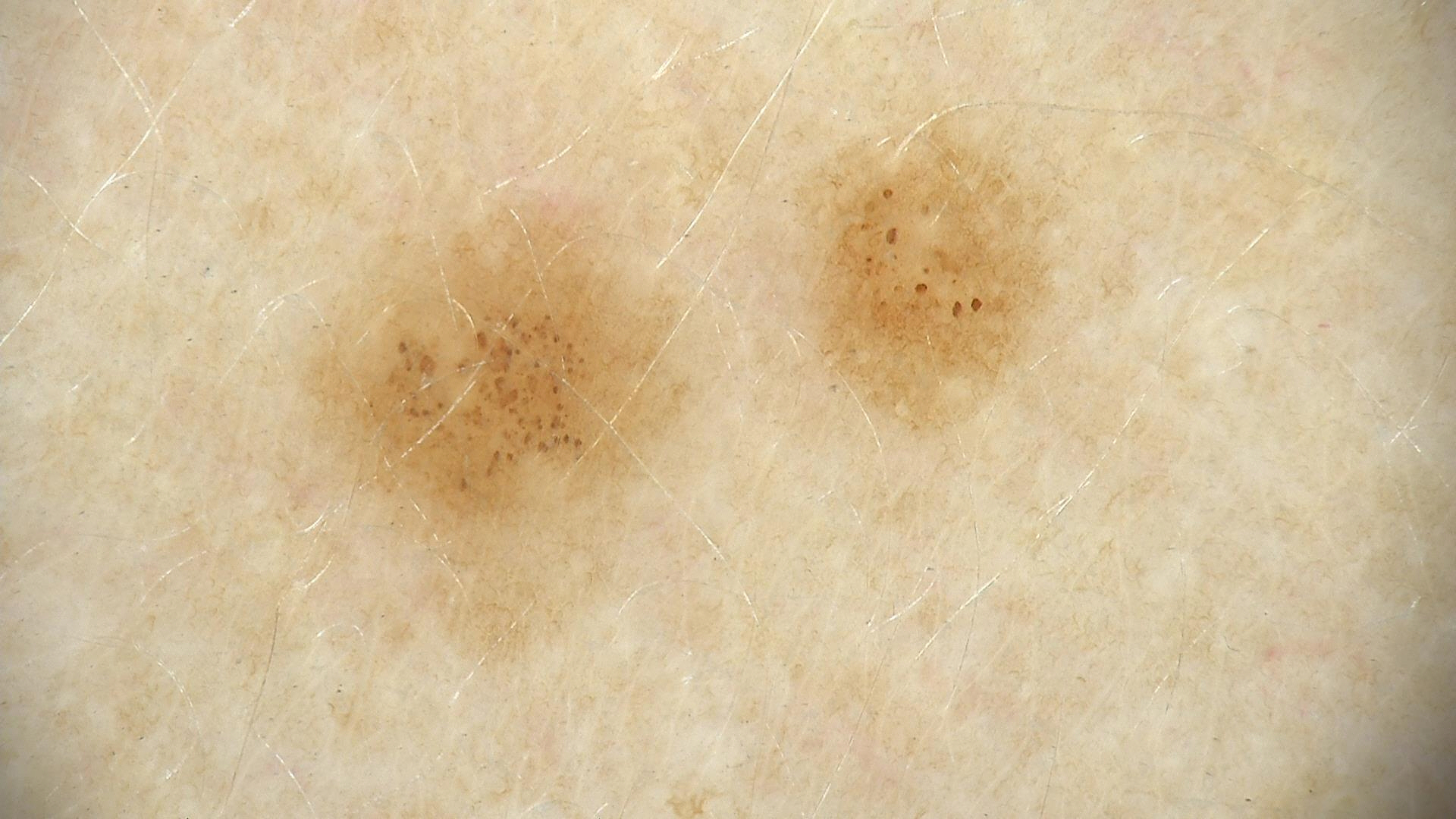Case:
• class: dysplastic junctional nevus (expert consensus)